Dermoscopy of a skin lesion.
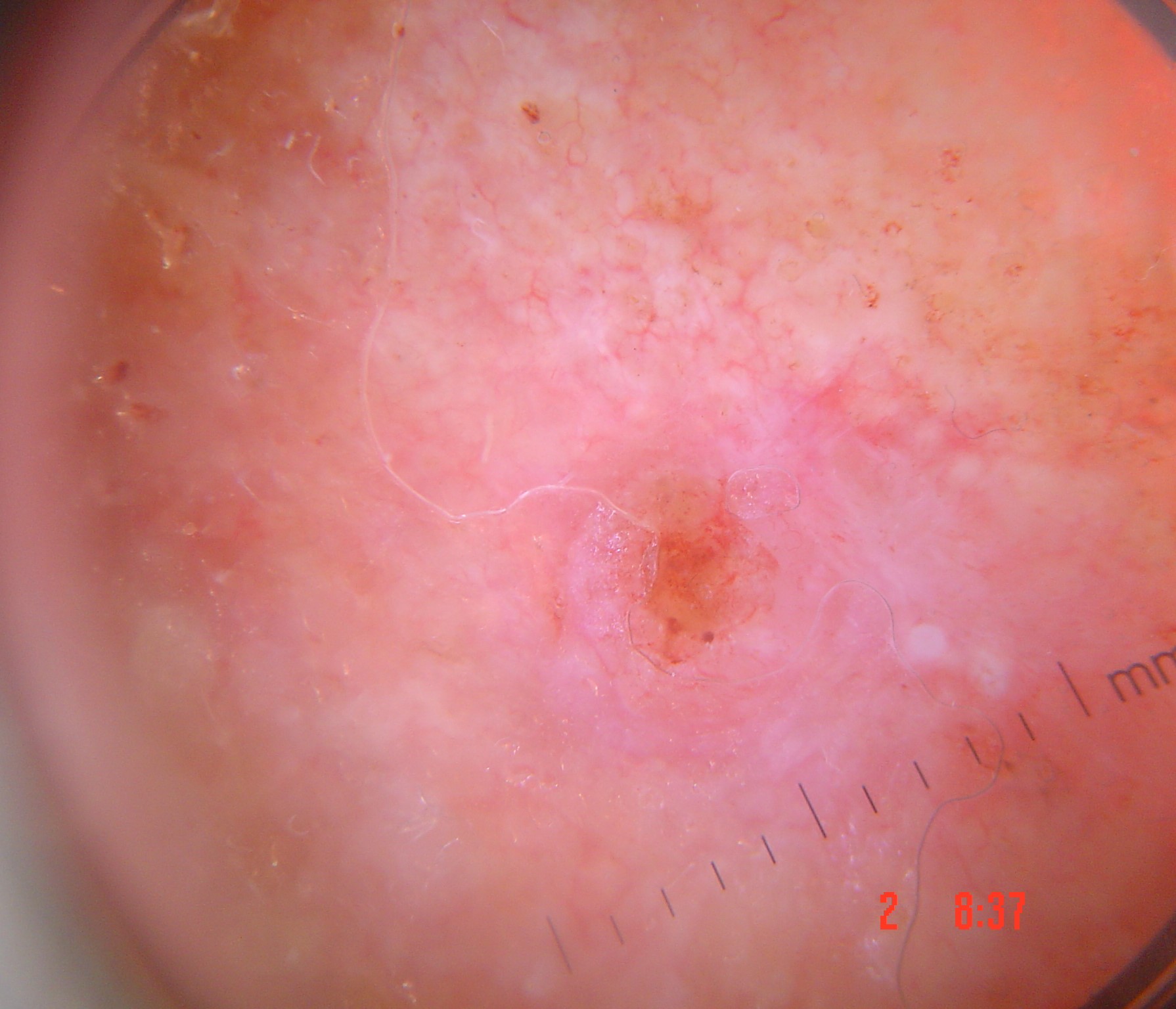classification — keratinocytic
diagnostic label — squamous cell carcinoma (biopsy-proven)